A dermoscopy image of a single skin lesion; a male subject, in their 50s: 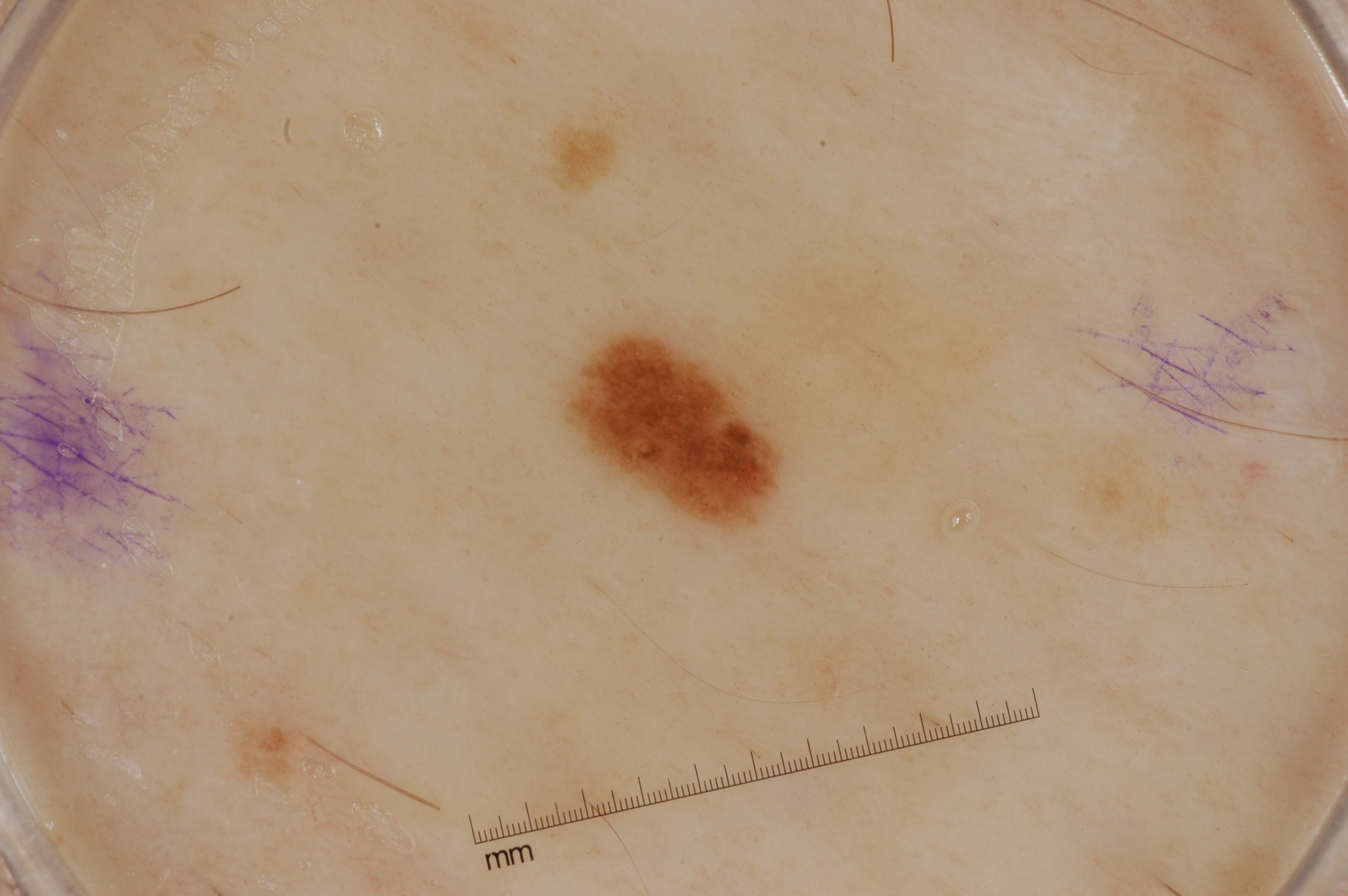Dermoscopy demonstrates no milia-like cysts, streaks, pigment network, or negative network. The lesion is bounded by x1=569 y1=322 x2=779 y2=525. Consistent with a melanocytic nevus.